The affected area is the leg. A close-up photograph.
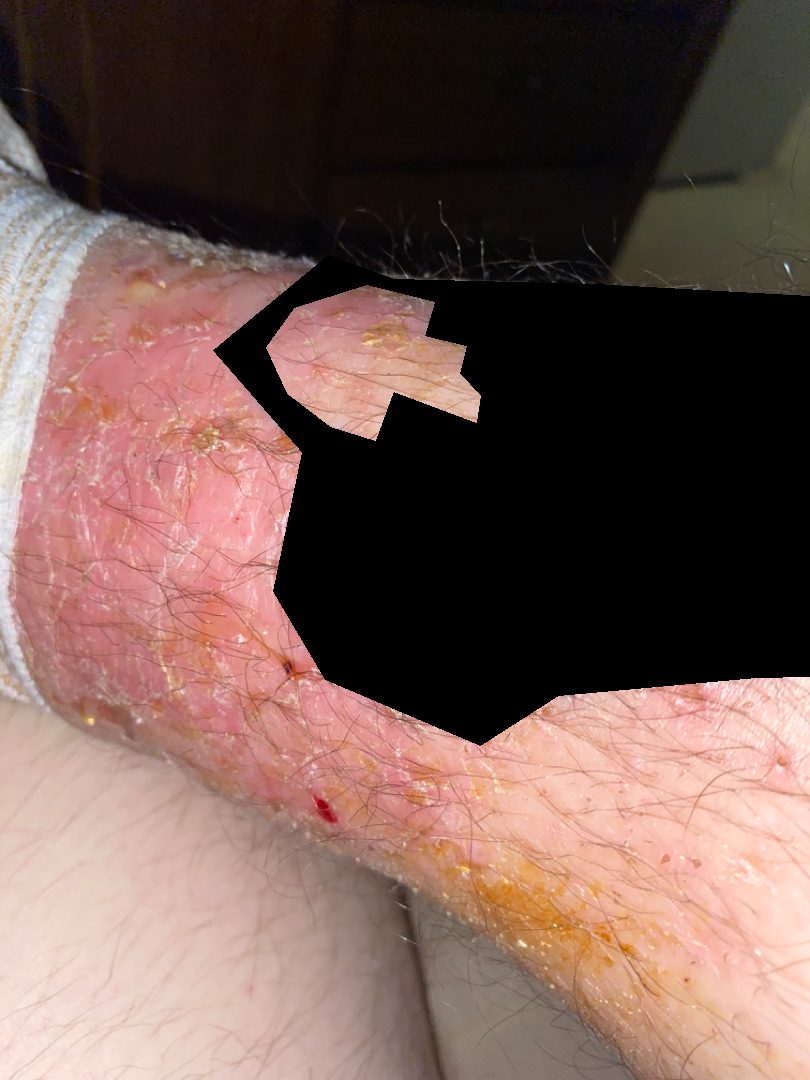A single dermatologist reviewed the case: the differential, in no particular order, includes Infected eczema and Stasis Dermatitis; a remote consideration is Cellulitis.